The photograph is a close-up of the affected area.
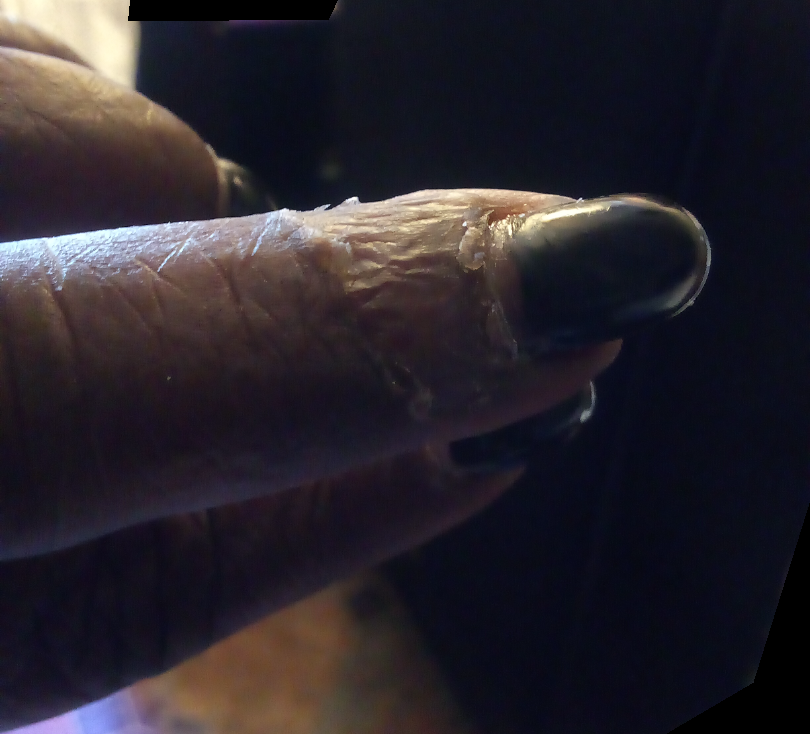The skin condition could not be confidently assessed from this image.